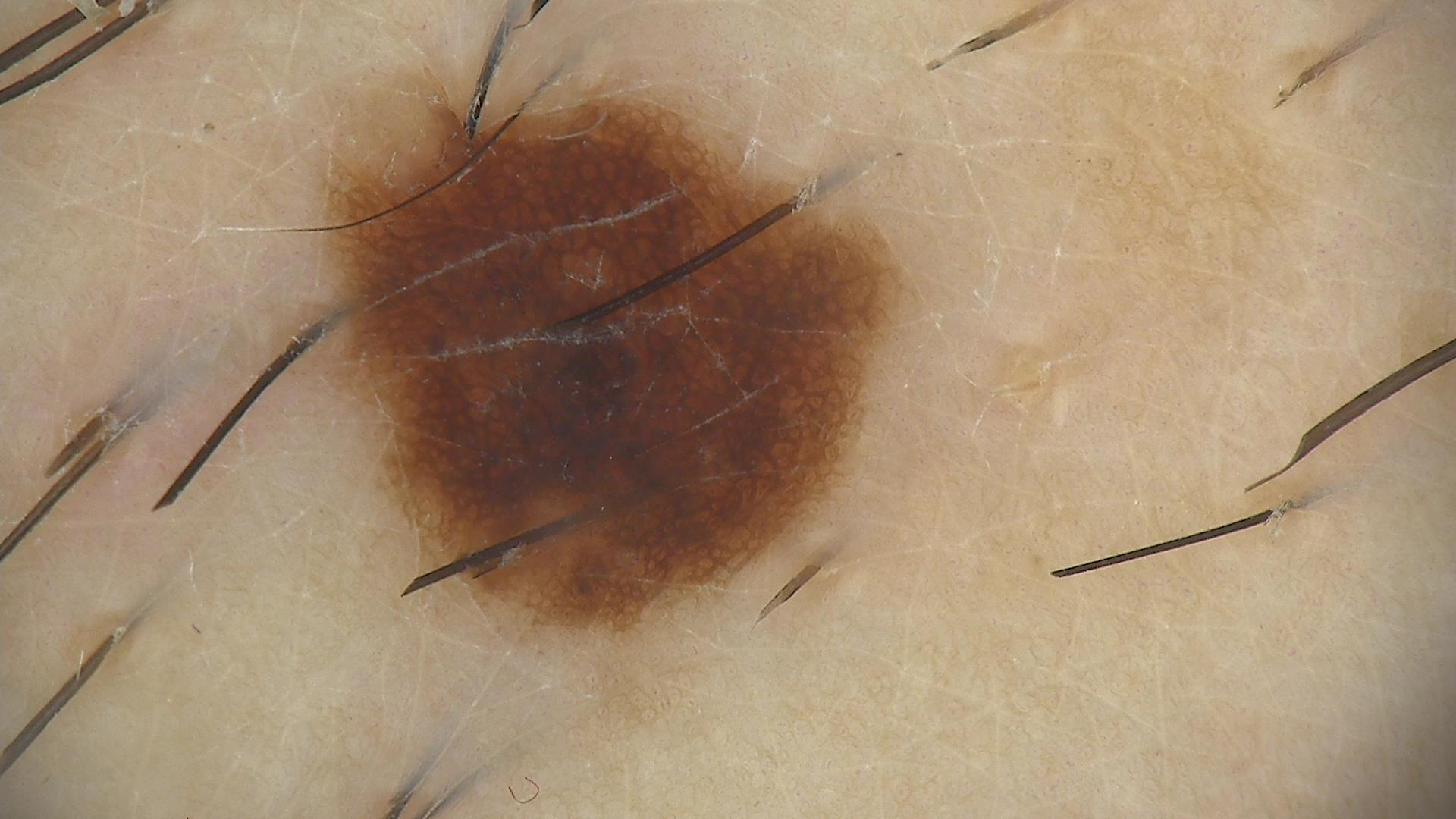| key | value |
|---|---|
| assessment | dysplastic junctional nevus (expert consensus) |